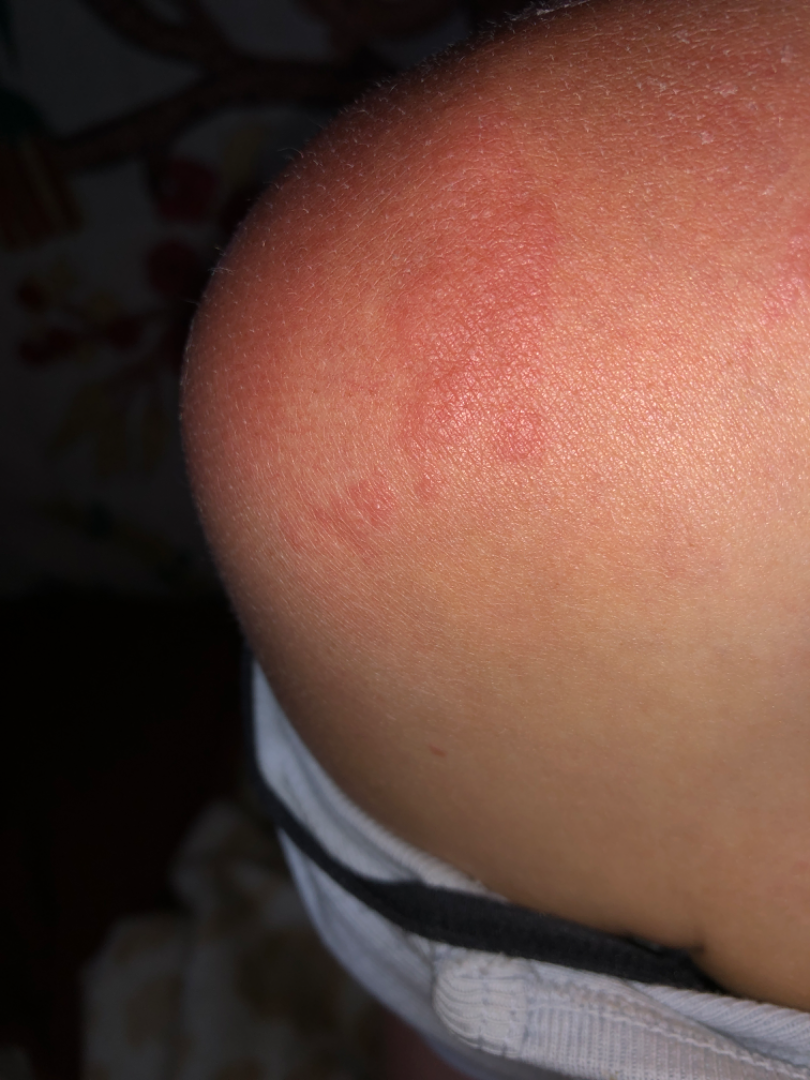{"assessment": "not assessable"}